This is a close-up image, Fitzpatrick skin type II; human graders estimated a Monk Skin Tone of 3 — 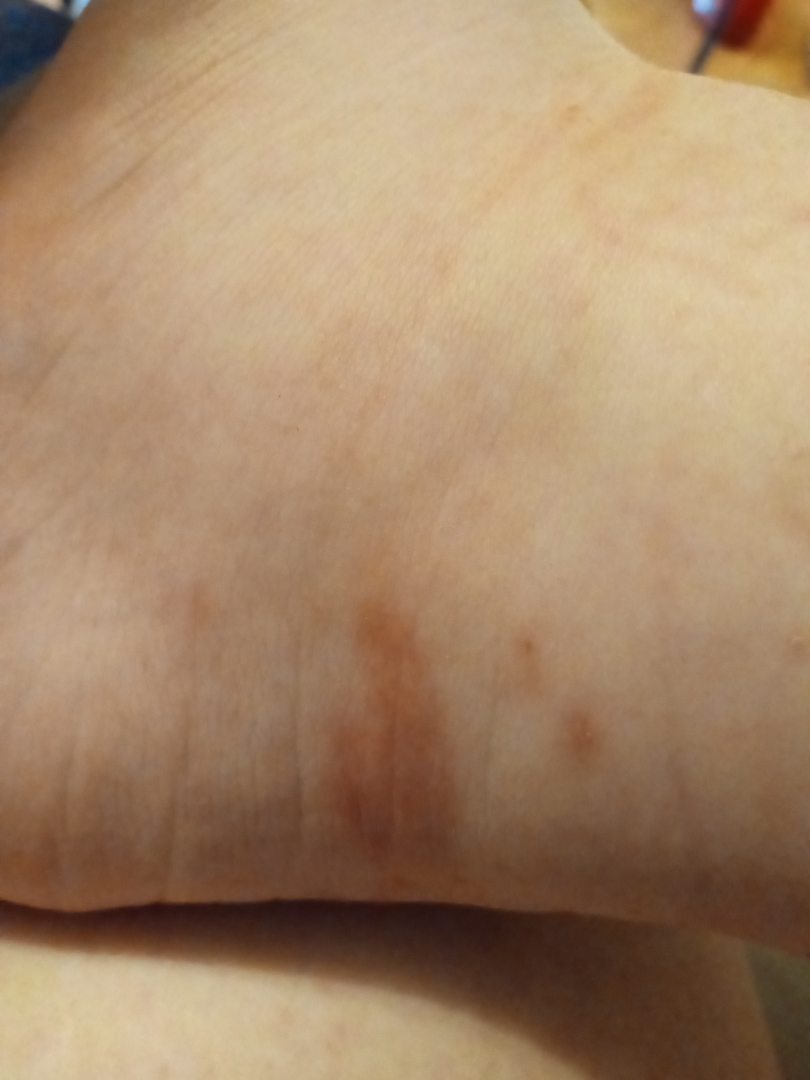| field | value |
|---|---|
| dermatologist impression | Pigmented purpuric eruption (possible); Kaposi's sarcoma of skin (possible) |